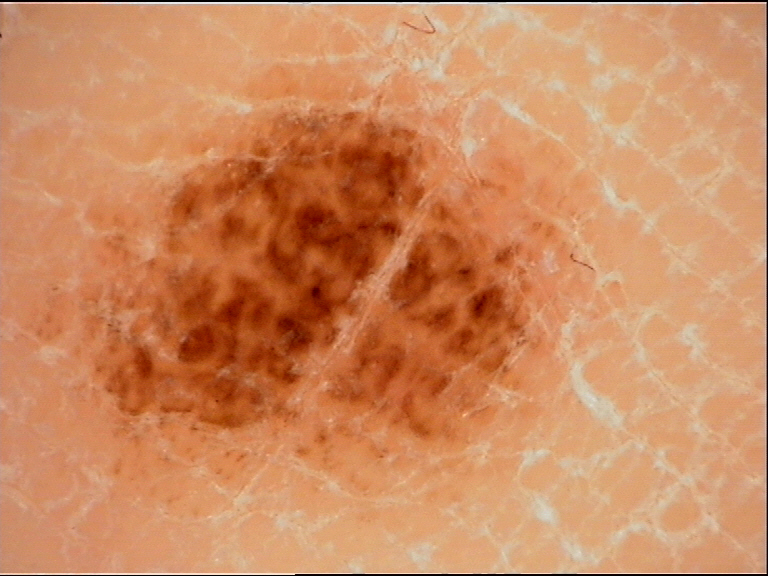| key | value |
|---|---|
| diagnosis | acral junctional nevus (expert consensus) |